Dermoscopy of a skin lesion; imaged for a research study, with no referral diagnosis recorded; a male patient 77 years of age.
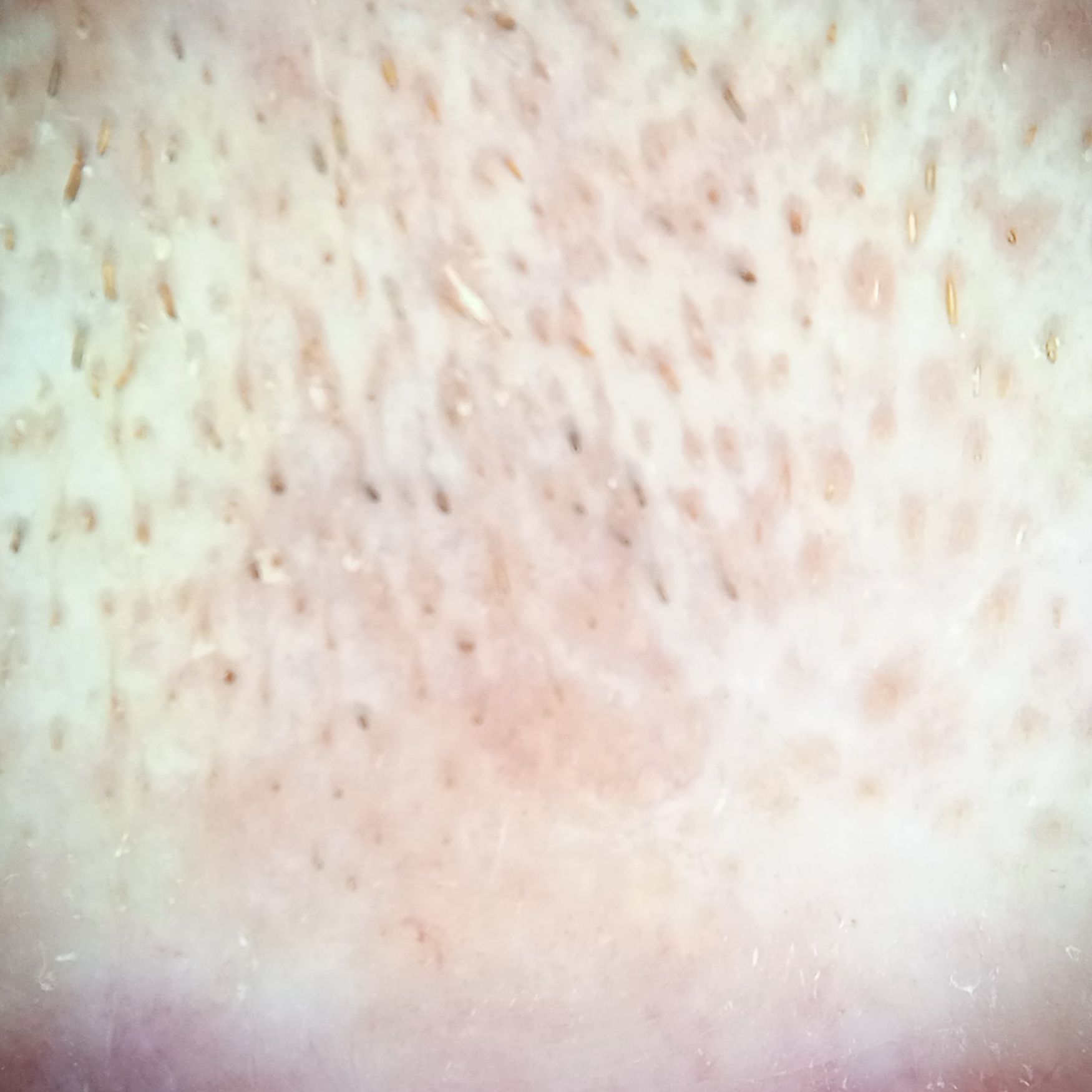Clinical context: The lesion is on the face. Measuring roughly 6.4 mm. Assessment: The diagnostic impression was an actinic keratosis.